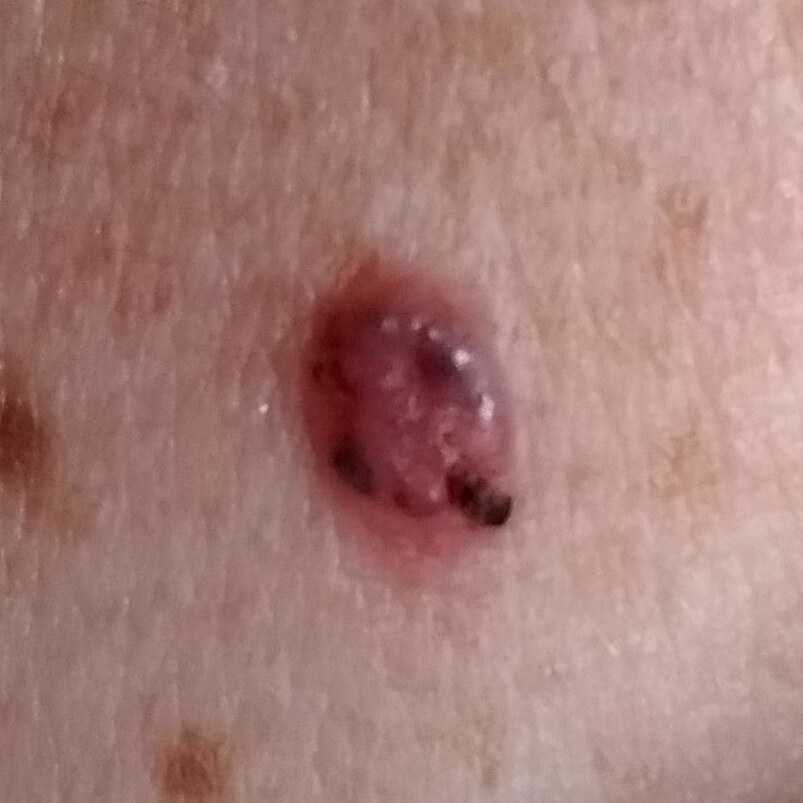{"skin_type": "III", "image": "clinical photograph", "risk_factors": {"positive": ["prior skin cancer (patient or family)", "prior cancer (patient or family)"]}, "patient": {"age": 43, "gender": "female"}, "lesion_size": {"diameter_1_mm": 4.0, "diameter_2_mm": 3.0}, "diagnosis": {"name": "basal cell carcinoma", "code": "BCC", "malignancy": "malignant", "confirmation": "histopathology"}}